The arm is involved; an image taken at an angle.
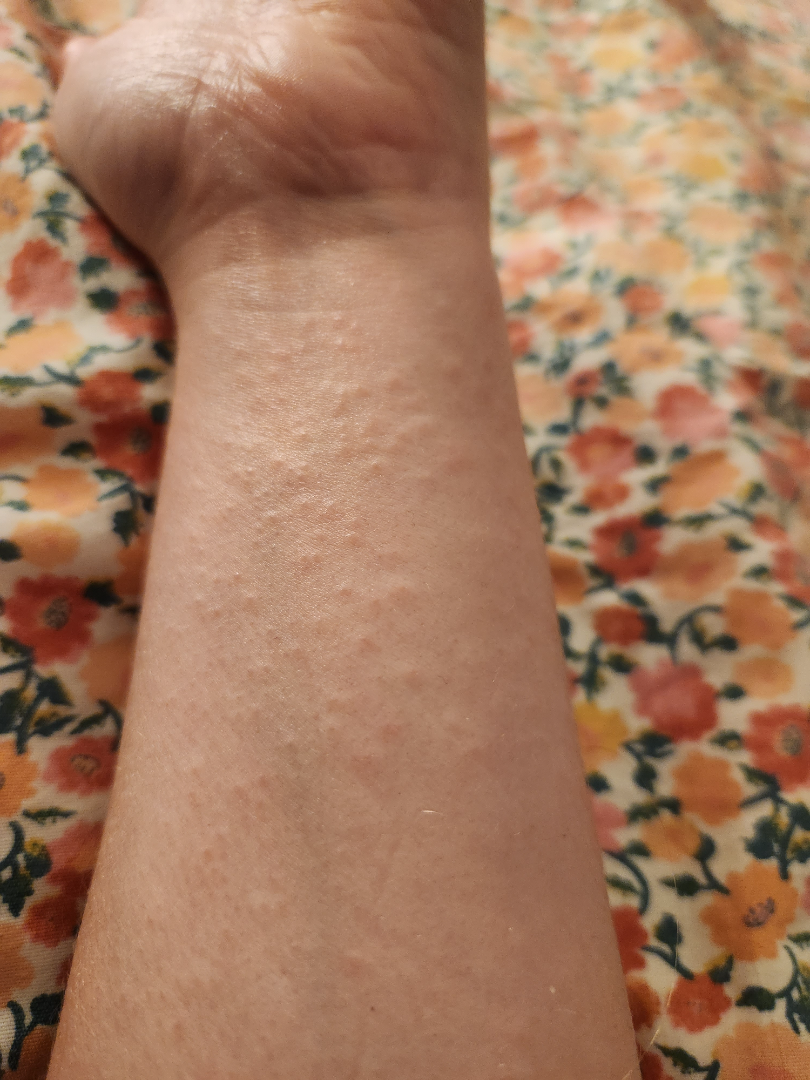The skin condition could not be confidently assessed from this image.
Reported duration is less than one week.
Symptoms reported: itching.
No associated systemic symptoms reported.
The patient considered this a rash.